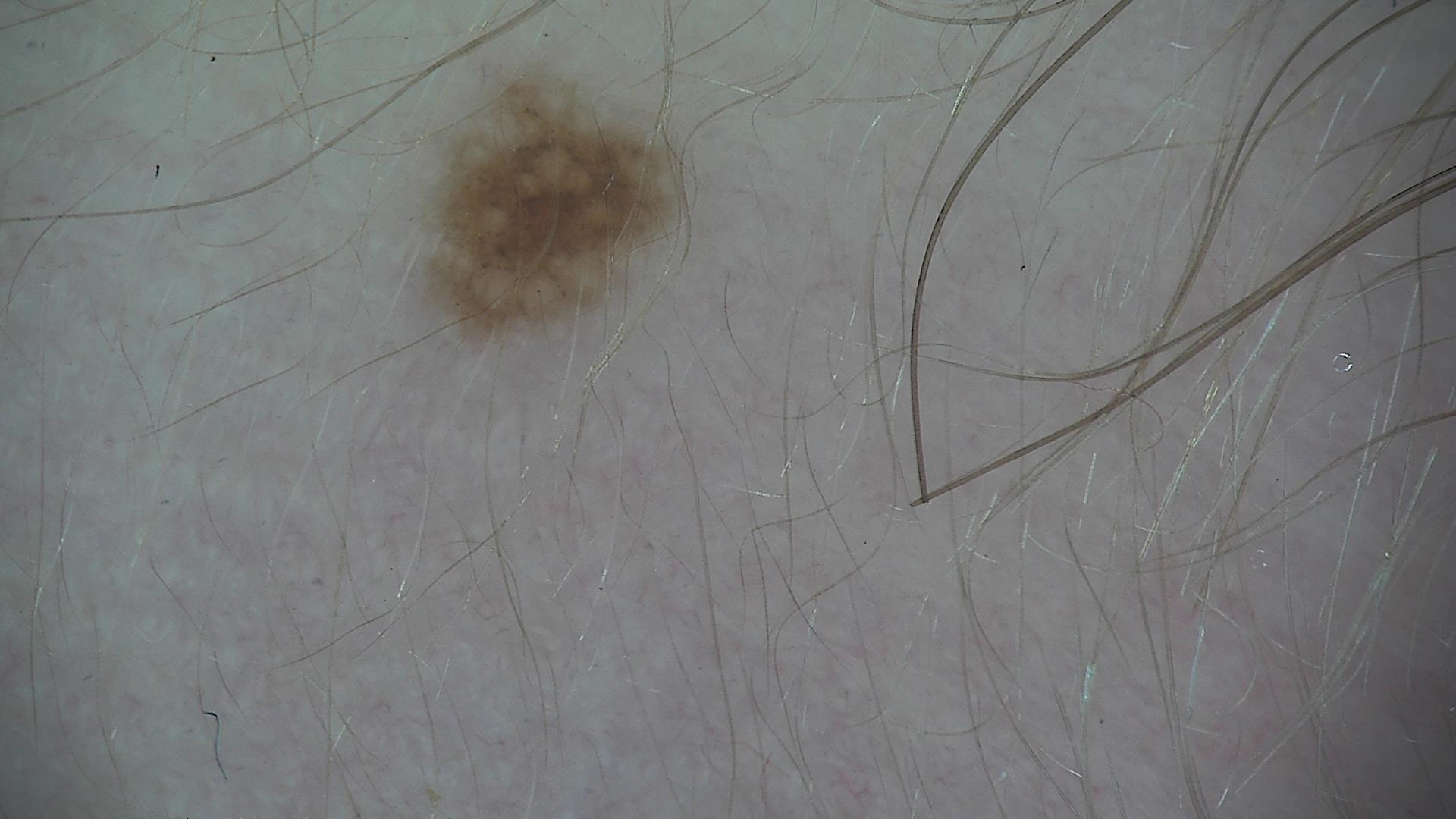Q: What is this lesion?
A: dysplastic junctional nevus (expert consensus)